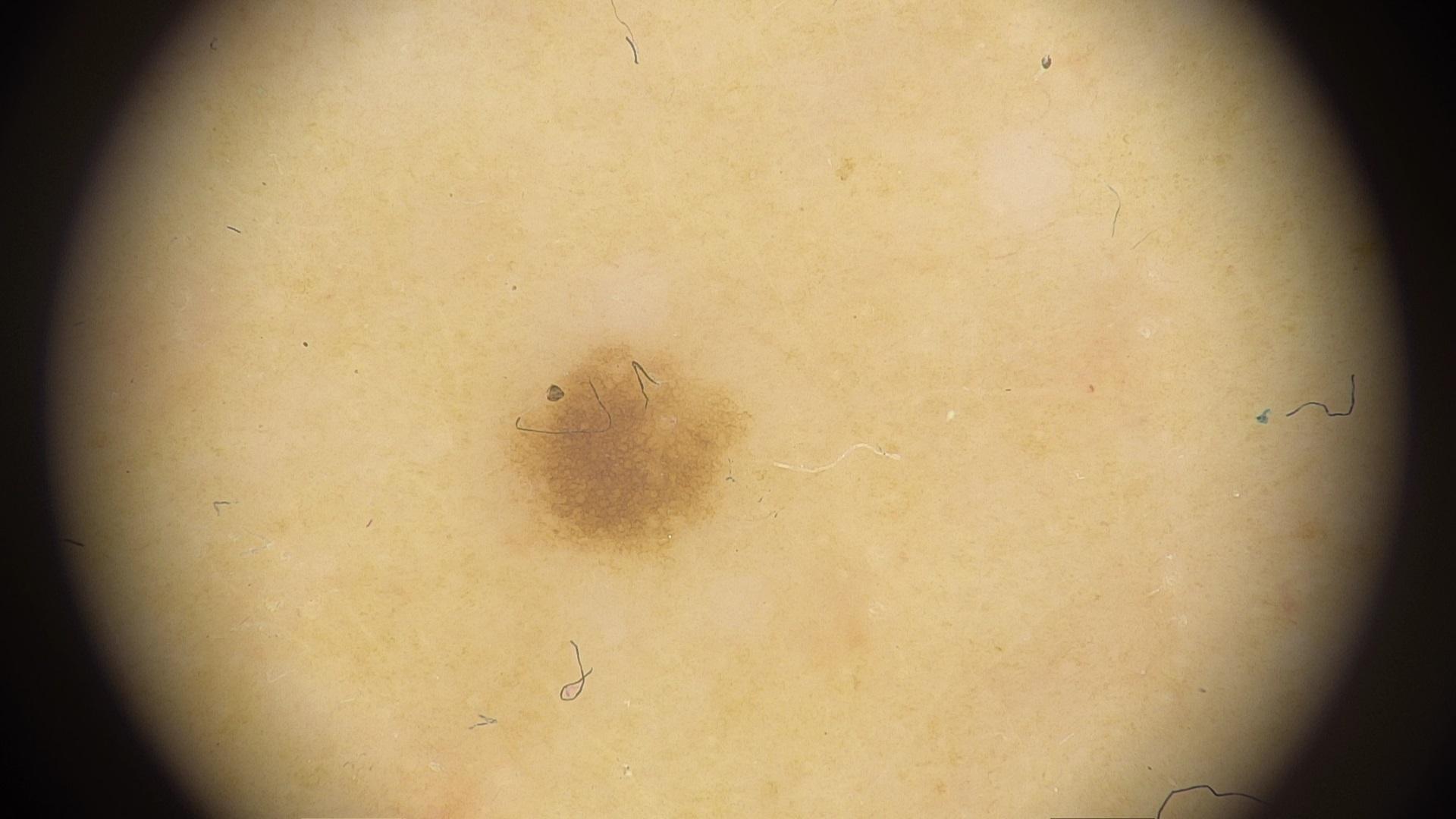A female patient aged approximately 50. The chart notes a prior melanoma but no first-degree relative with melanoma. A skin lesion imaged with contact-polarized dermoscopy. The patient was assessed as Fitzpatrick II. The lesion is on a lower extremity. The clinical assessment was a benign lesion — a nevus.